A male subject in their mid- to late 80s or older · a contact-polarized dermoscopy image of a skin lesion:
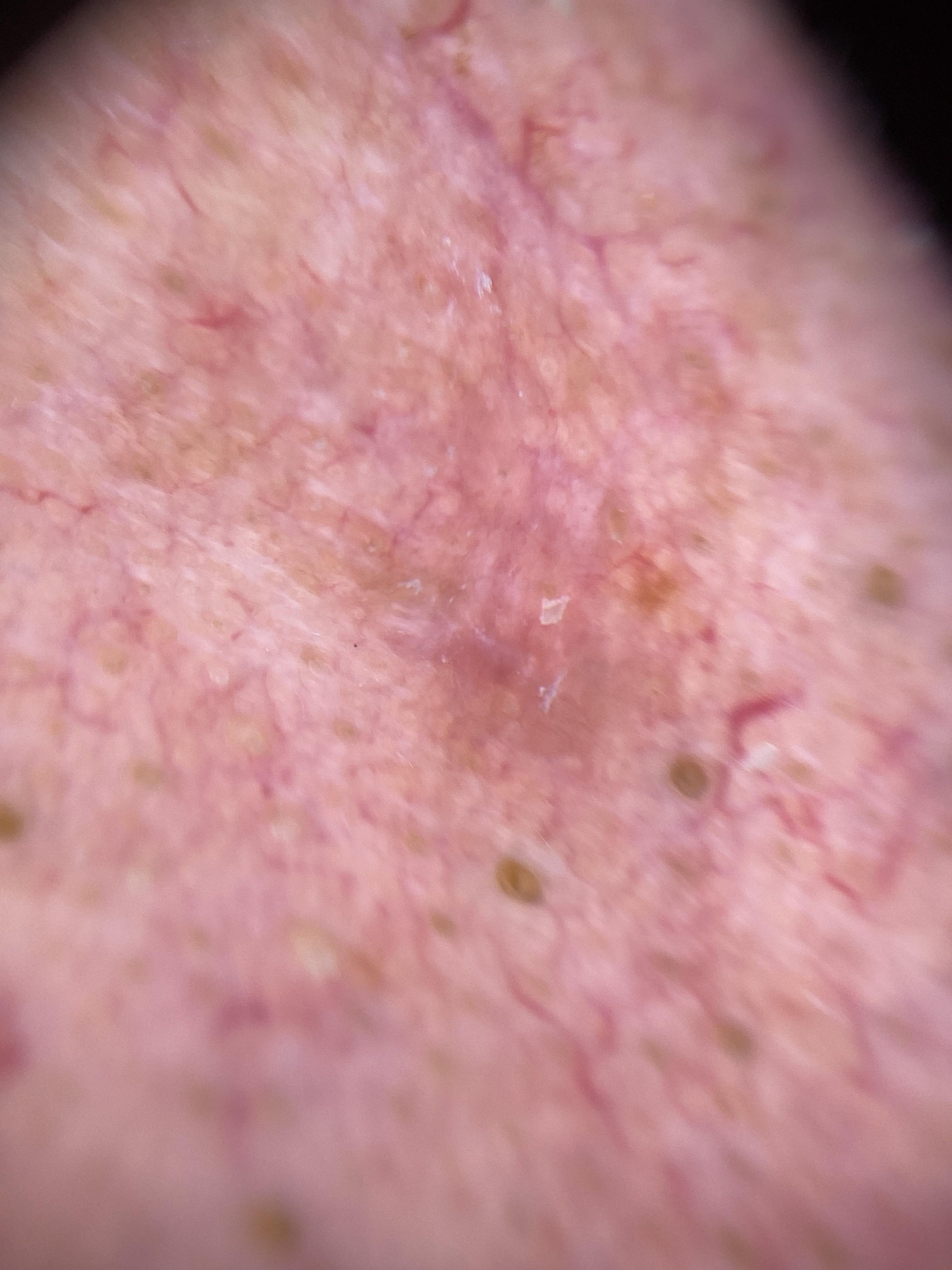Q: Where on the body is the lesion?
A: the head or neck
Q: What is this lesion?
A: Basal cell carcinoma (biopsy-proven)